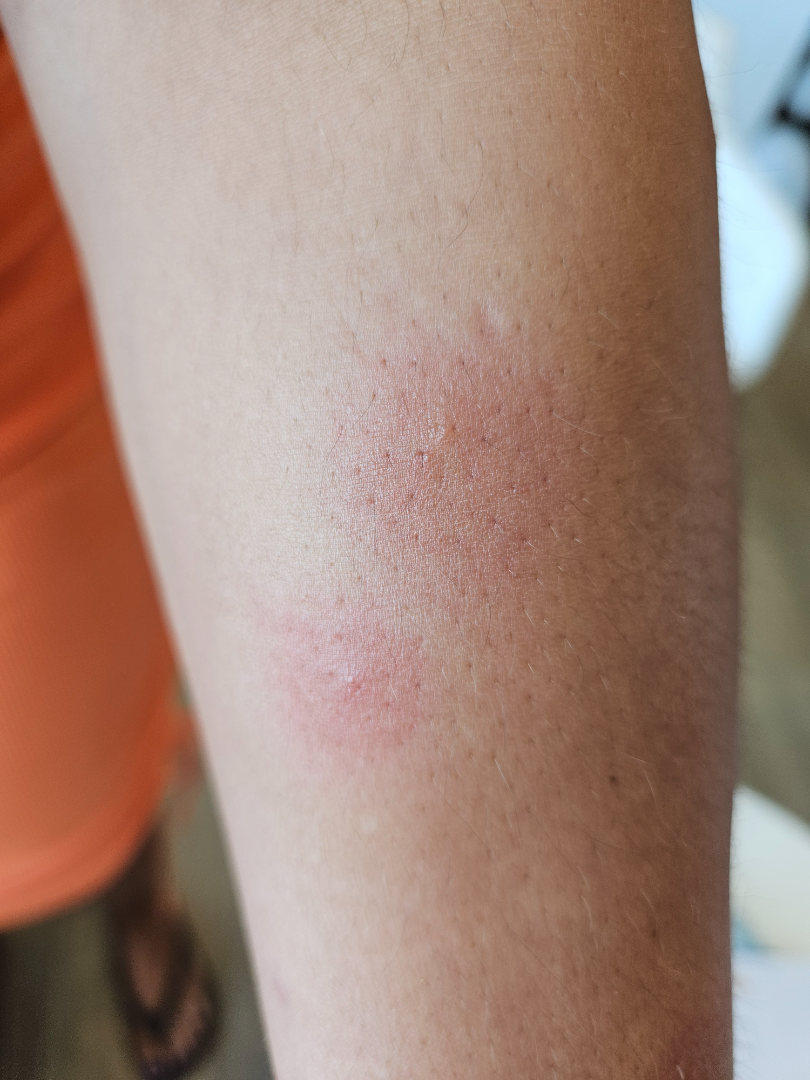The reviewing dermatologist was unable to assign a differential diagnosis from the image.
A close-up photograph.